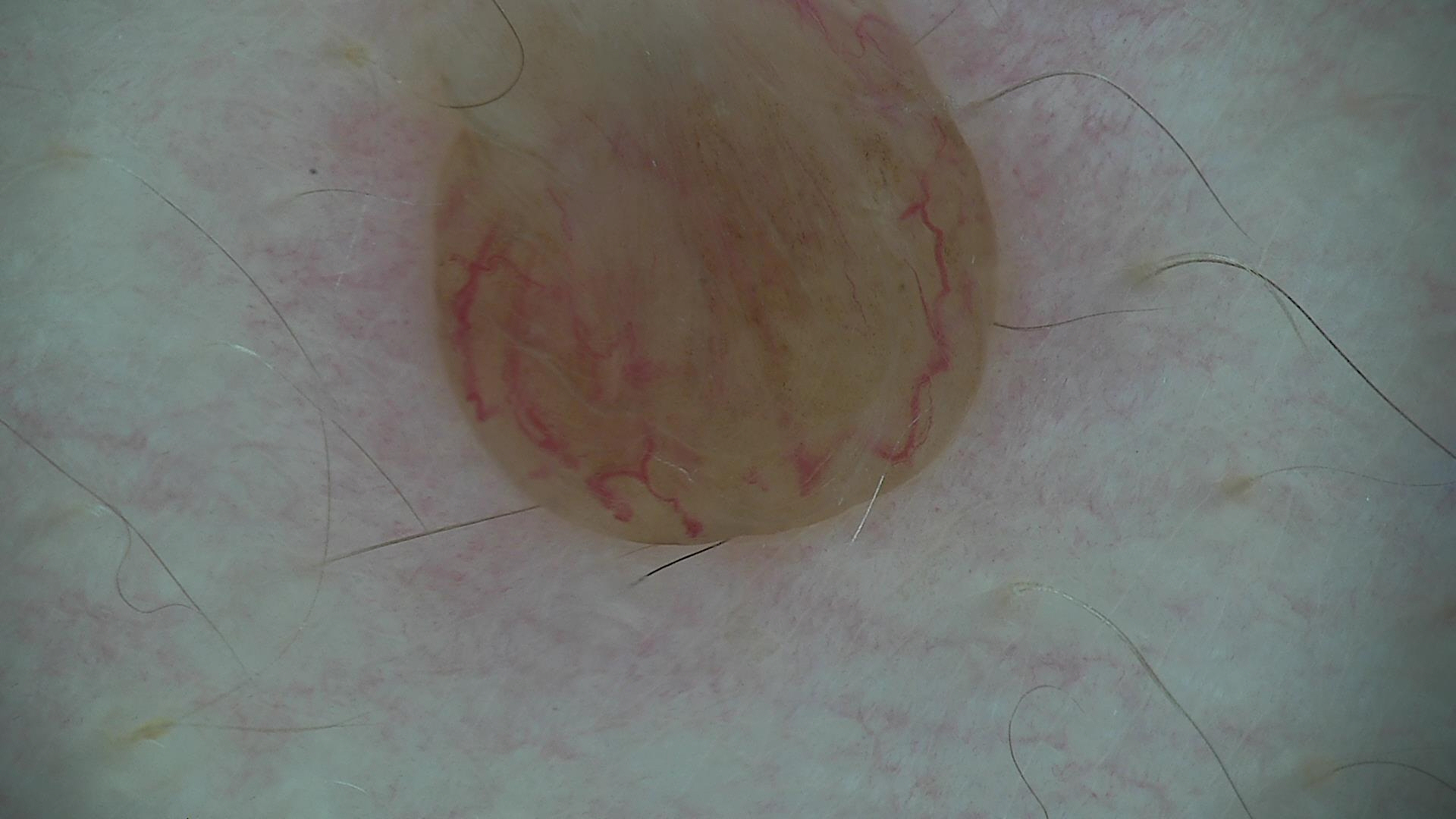Dermoscopy of a skin lesion. Classified as a dermal nevus.